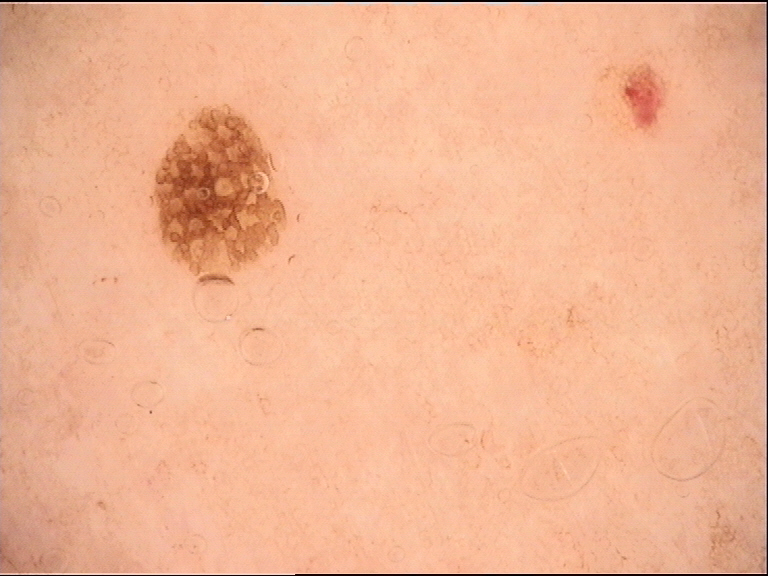<lesion>
<image>dermoscopy</image>
<lesion_type>
<main_class>keratinocytic</main_class>
</lesion_type>
<diagnosis>
<name>seborrheic keratosis</name>
<code>sk</code>
<malignancy>benign</malignancy>
<super_class>non-melanocytic</super_class>
<confirmation>expert consensus</confirmation>
</diagnosis>
</lesion>